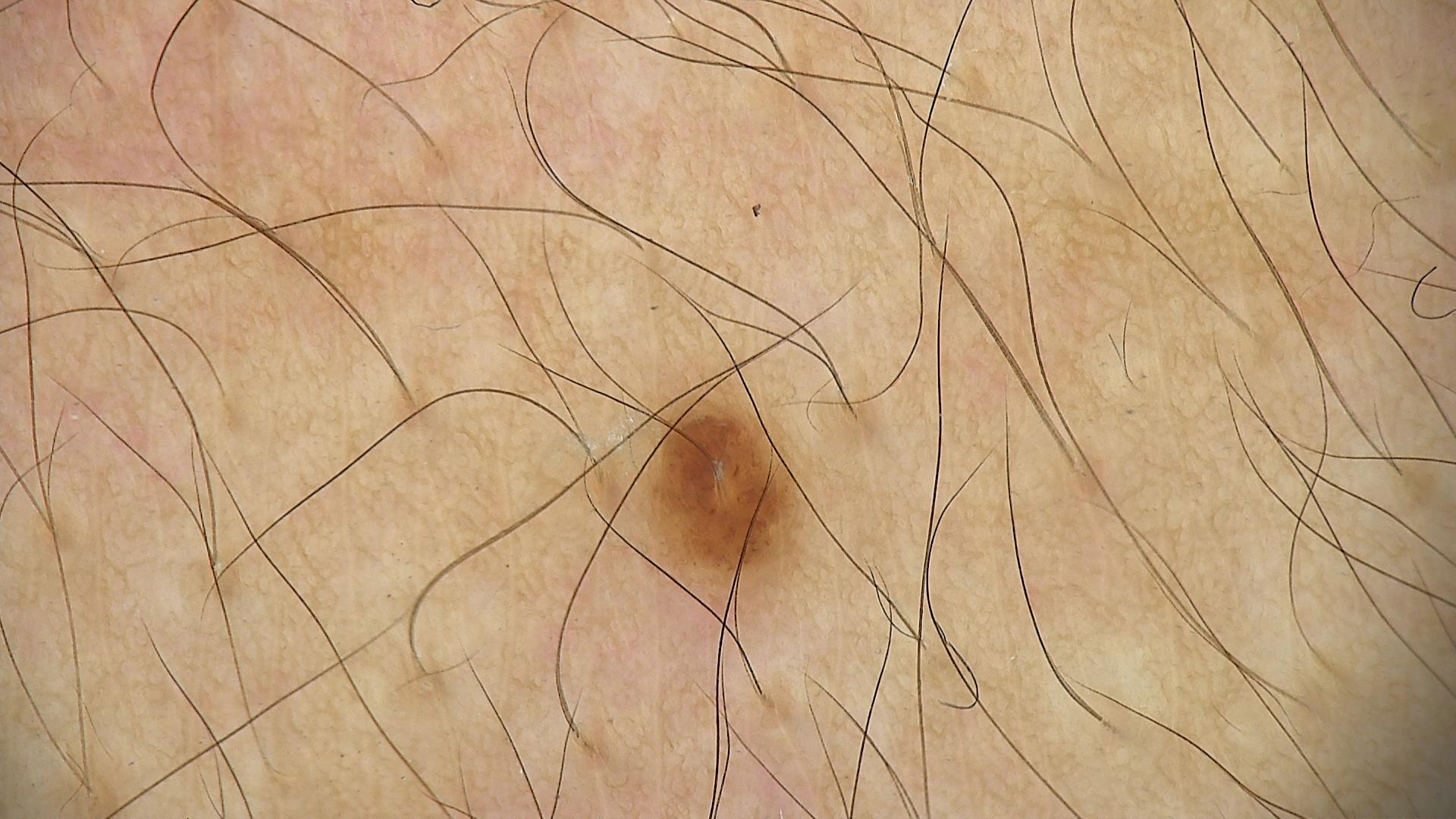  diagnosis:
    name: junctional nevus
    code: jb
    malignancy: benign
    super_class: melanocytic
    confirmation: expert consensus